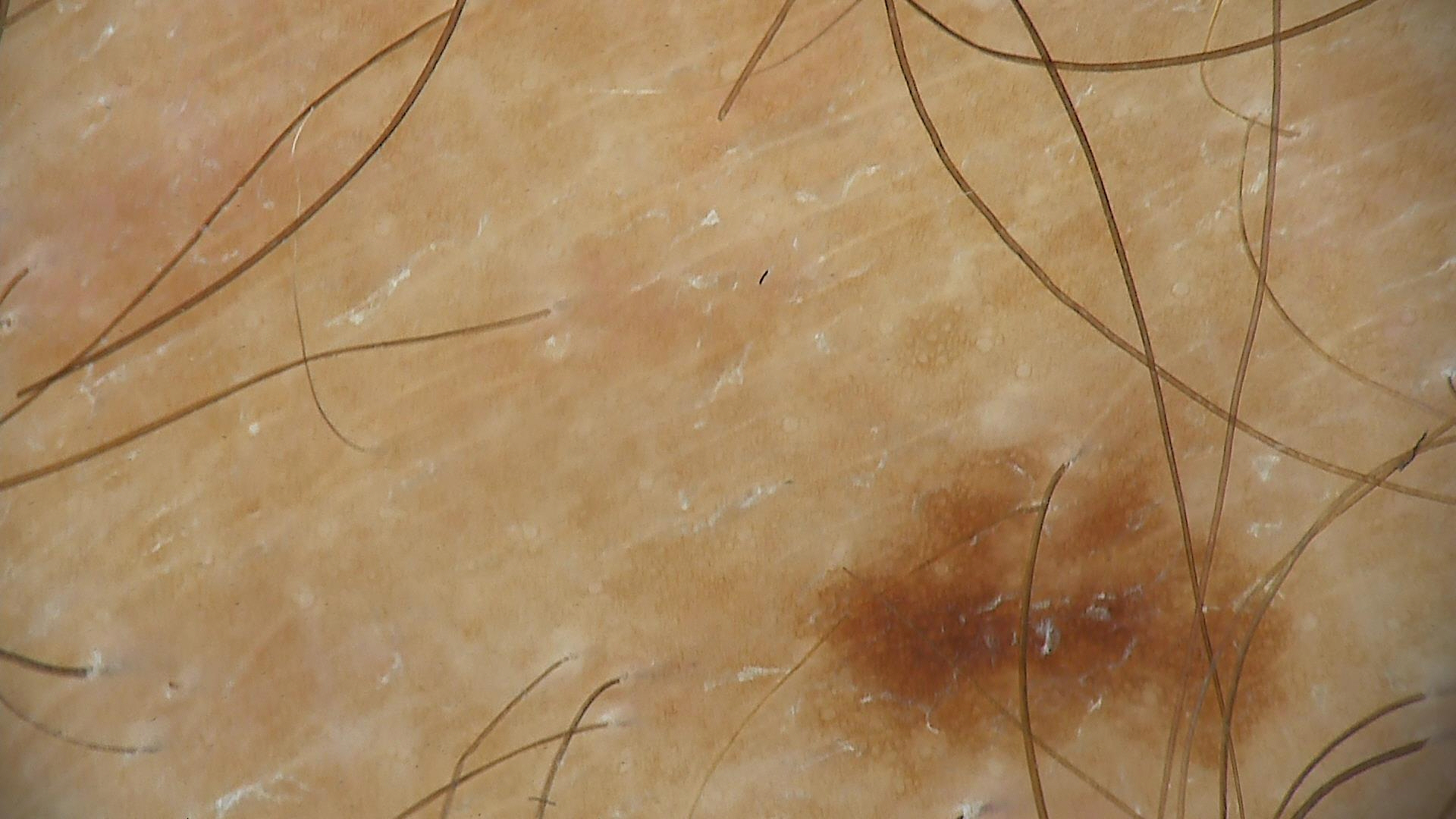diagnosis — dysplastic junctional nevus (expert consensus).